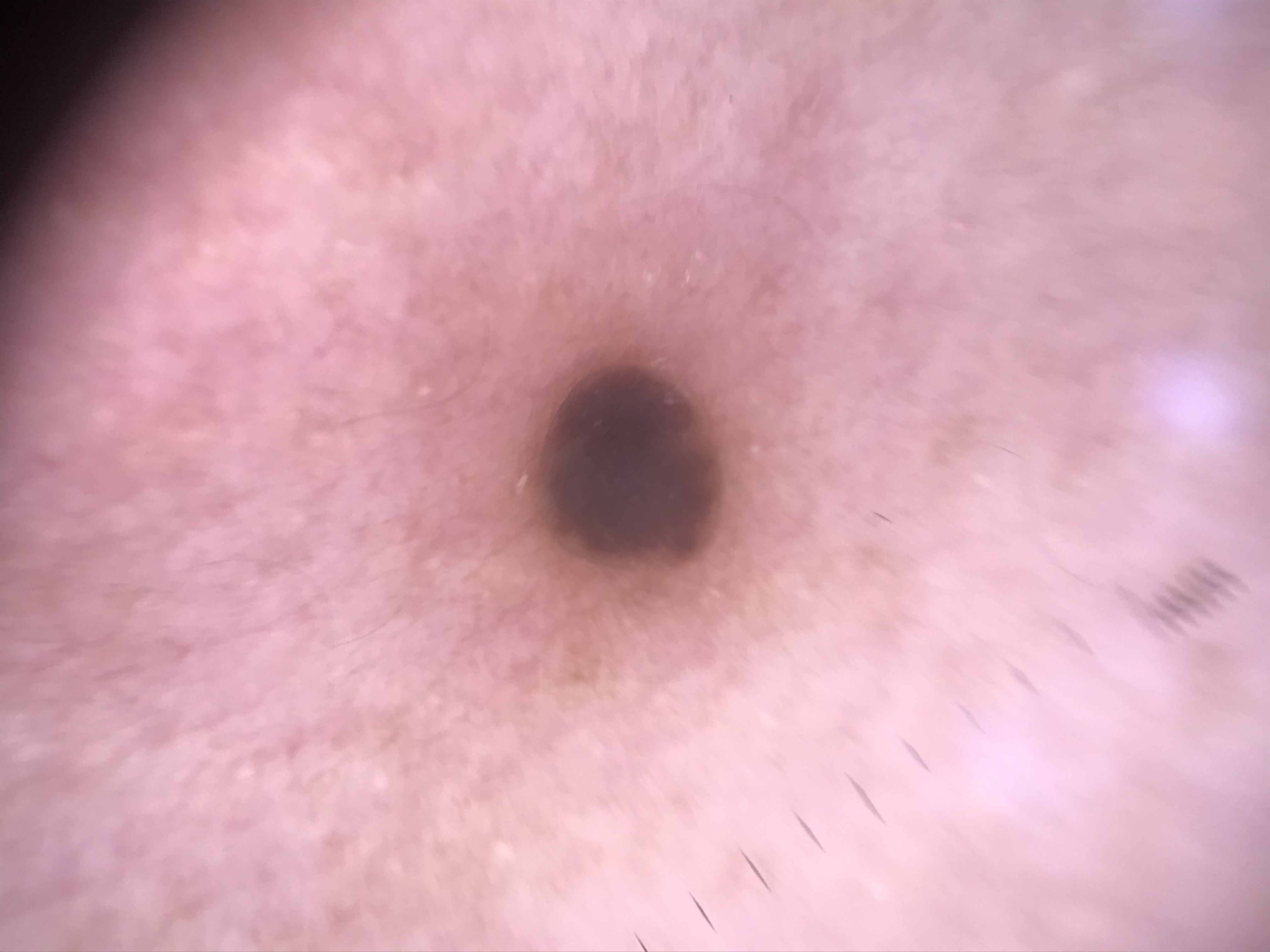Summary: A dermoscopy image of a single skin lesion. This is a banal lesion. Impression: The diagnosis was a compound nevus.